A subject in their early 80s · a clinical photograph of a skin lesion:
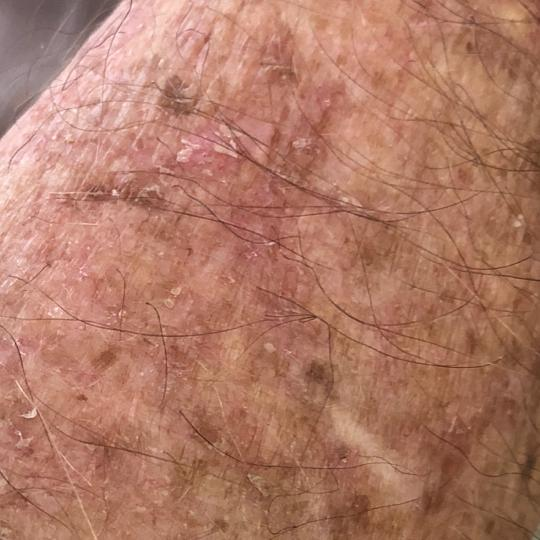lesion_location: a forearm
symptoms:
  present:
    - itching
  absent:
    - elevation
    - growth
diagnosis:
  name: actinic keratosis
  code: ACK
  malignancy: indeterminate
  confirmation: clinical consensus